The chart records melanoma in a first-degree relative but no prior melanoma; a female patient approximately 20 years of age; contact-polarized dermoscopy of a skin lesion.
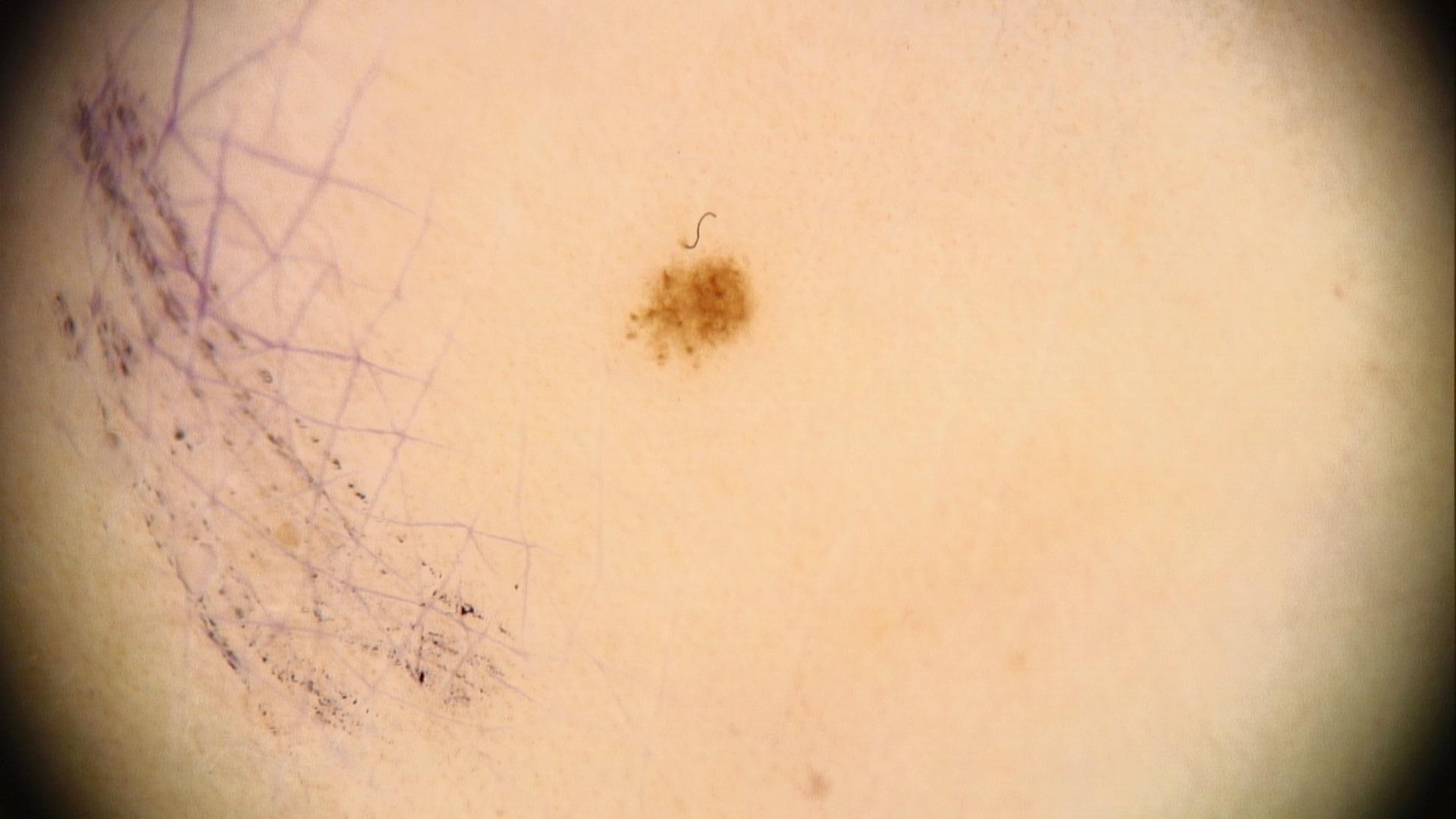site: a lower extremity, diagnostic label: Nevus (clinical impression).